The chart records a previous melanoma. A wide-field clinical photograph of a skin lesion. A male patient aged 78-82. The patient is FST II — 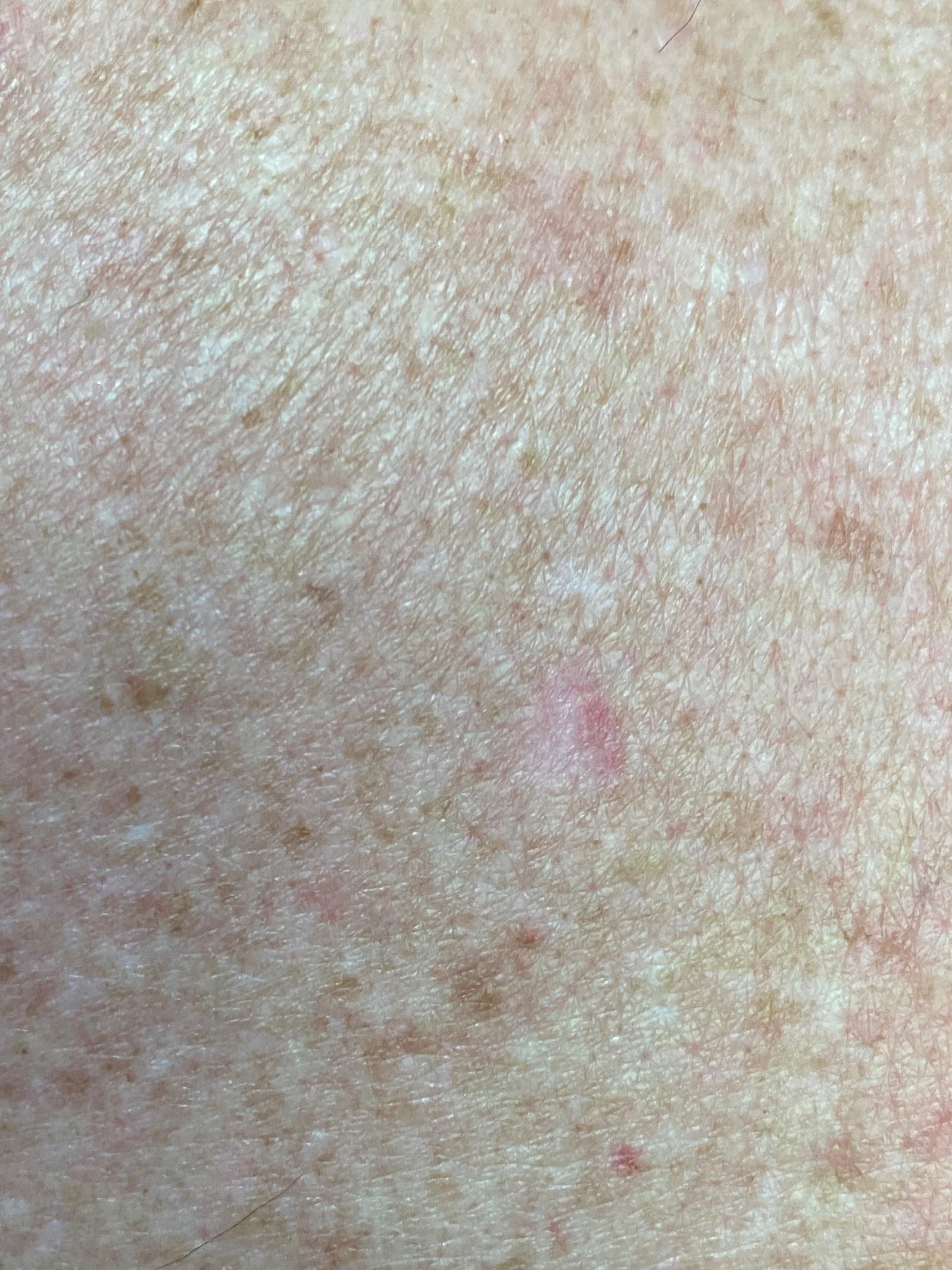diagnosis = Basal cell carcinoma (biopsy-proven).